Dermoscopy of a skin lesion:
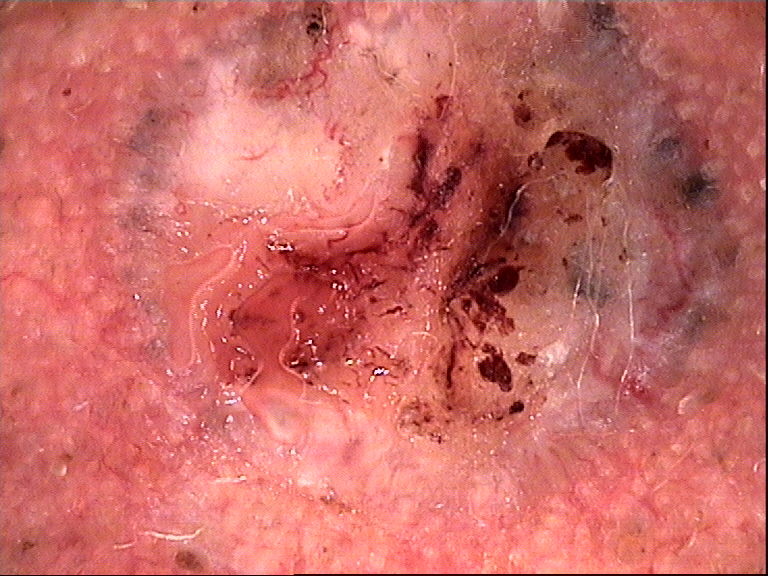This is a keratinocytic lesion. Confirmed on histopathology as a basal cell carcinoma.